A male patient, approximately 65 years of age. Dermoscopy of a skin lesion — 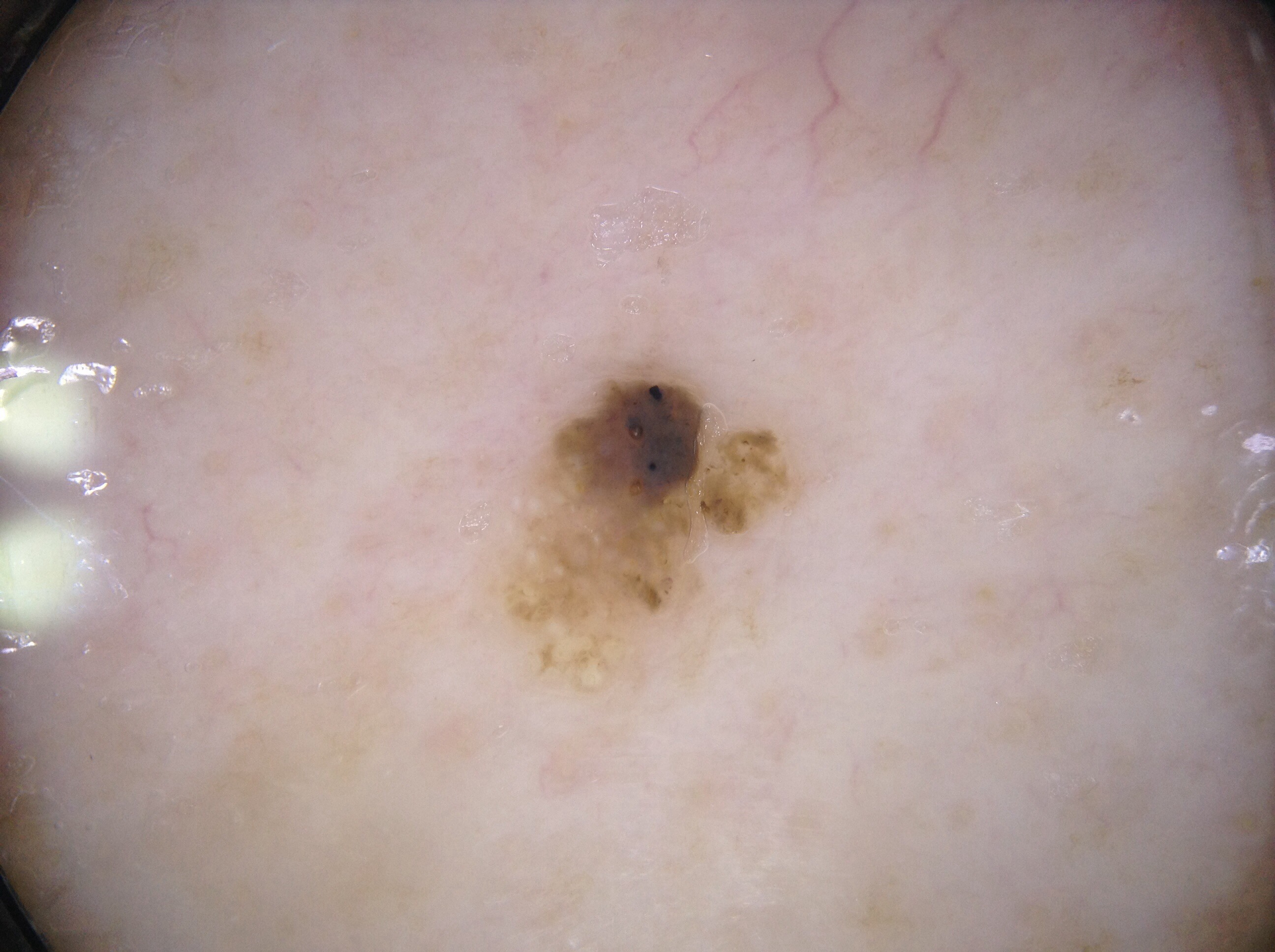Findings:
– lesion bbox: box(529, 365, 797, 632)
– dermoscopic findings: milia-like cysts
– diagnostic label: a seborrheic keratosis, a benign skin lesion